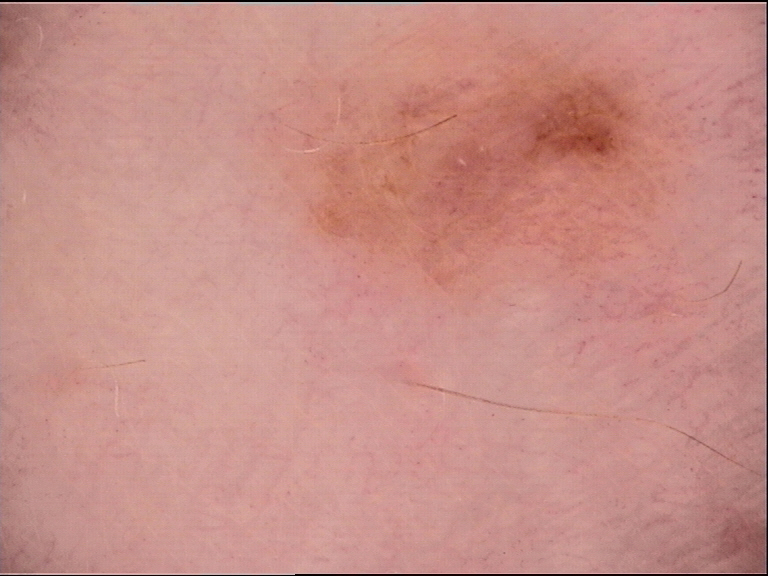modality — dermatoscopy; lesion type — banal; assessment — junctional nevus (expert consensus).